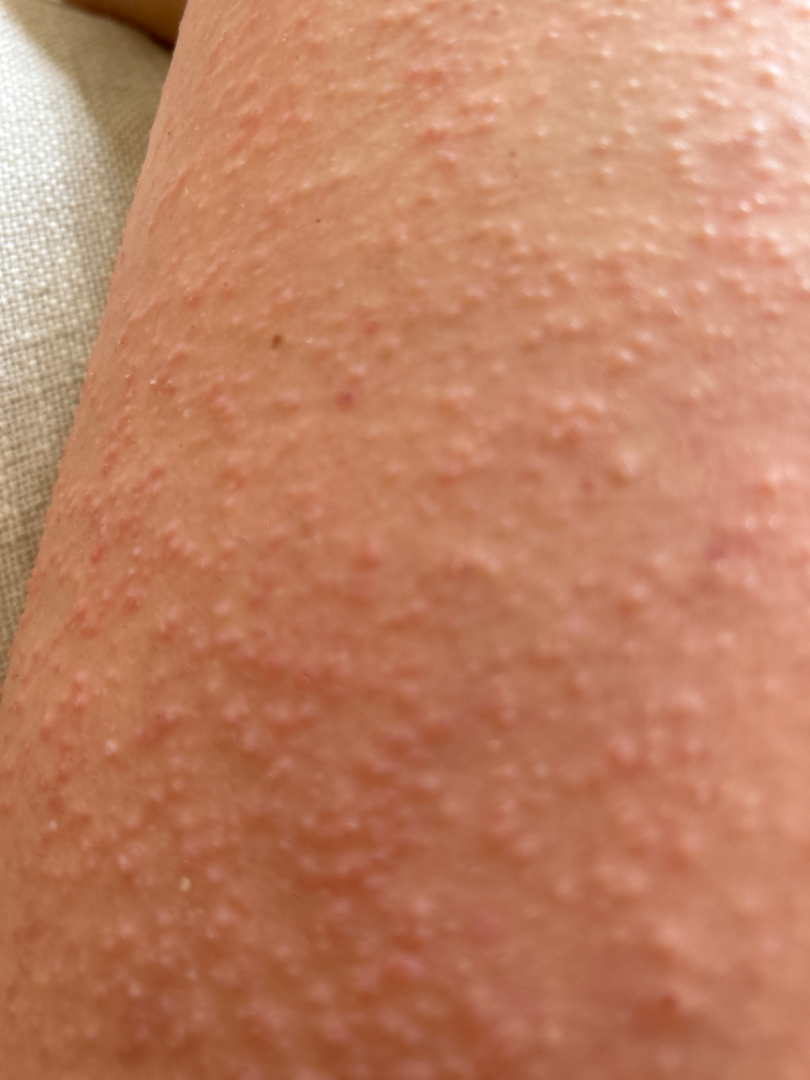Impression:
The condition could not be reliably identified from the image.